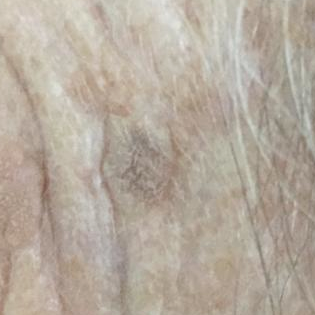| feature | finding |
|---|---|
| modality | clinical photograph |
| site | the face |
| patient-reported symptoms | elevation |
| diagnostic label | seborrheic keratosis (clinical consensus) |